The subject is 60–69, female · the photograph was taken at an angle · the leg is involved — 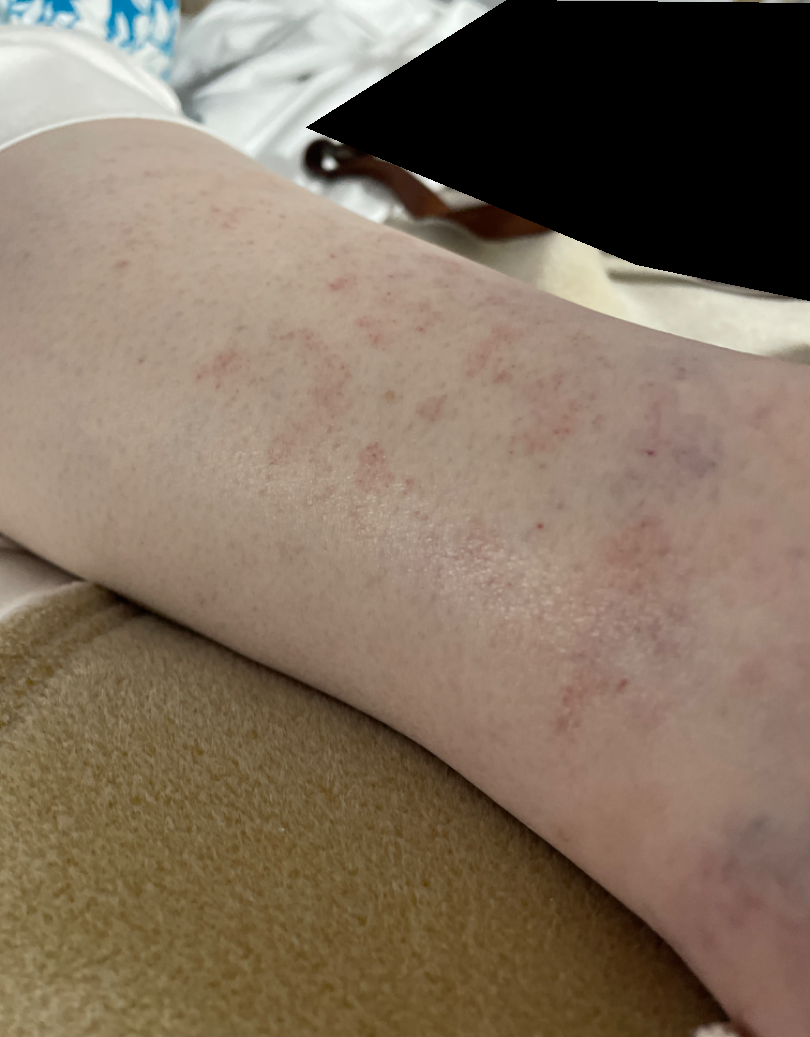patient describes the issue as = a rash | onset = about one day | surface texture = flat | symptoms = bothersome appearance | differential diagnosis = the leading consideration is Pigmented purpuric eruption; less probable is Leukocytoclastic Vasculitis.